A dermoscopic close-up of a skin lesion.
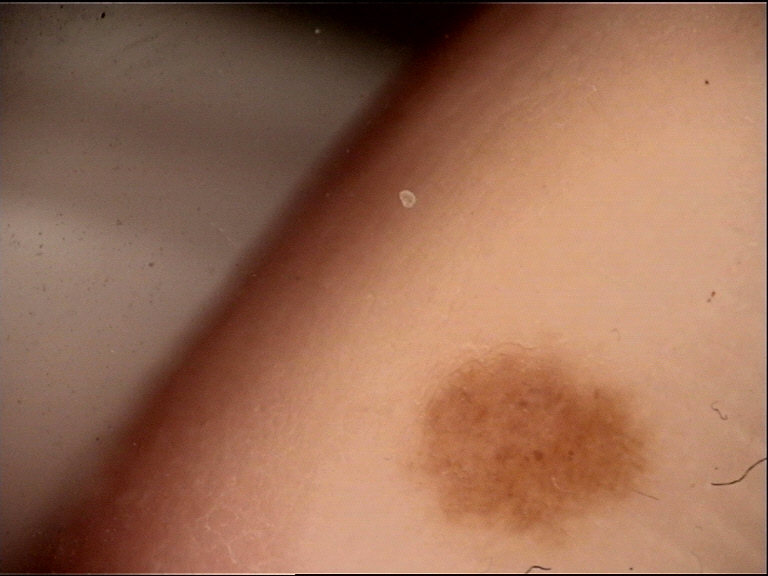This is a banal lesion. Labeled as a junctional nevus.